FST III · the photograph was taken at a distance:
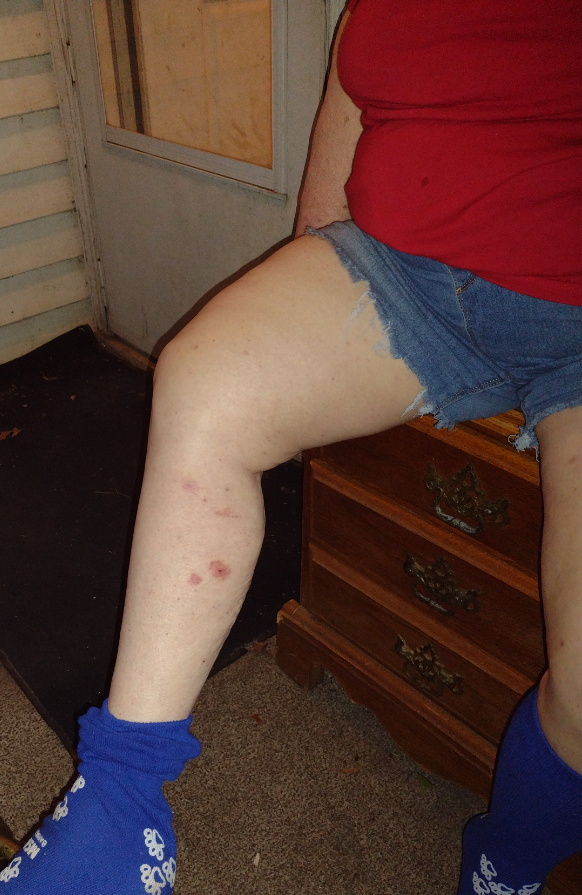Reviewed remotely by one dermatologist: most likely Pigmented purpuric eruption; also raised was Purpura.